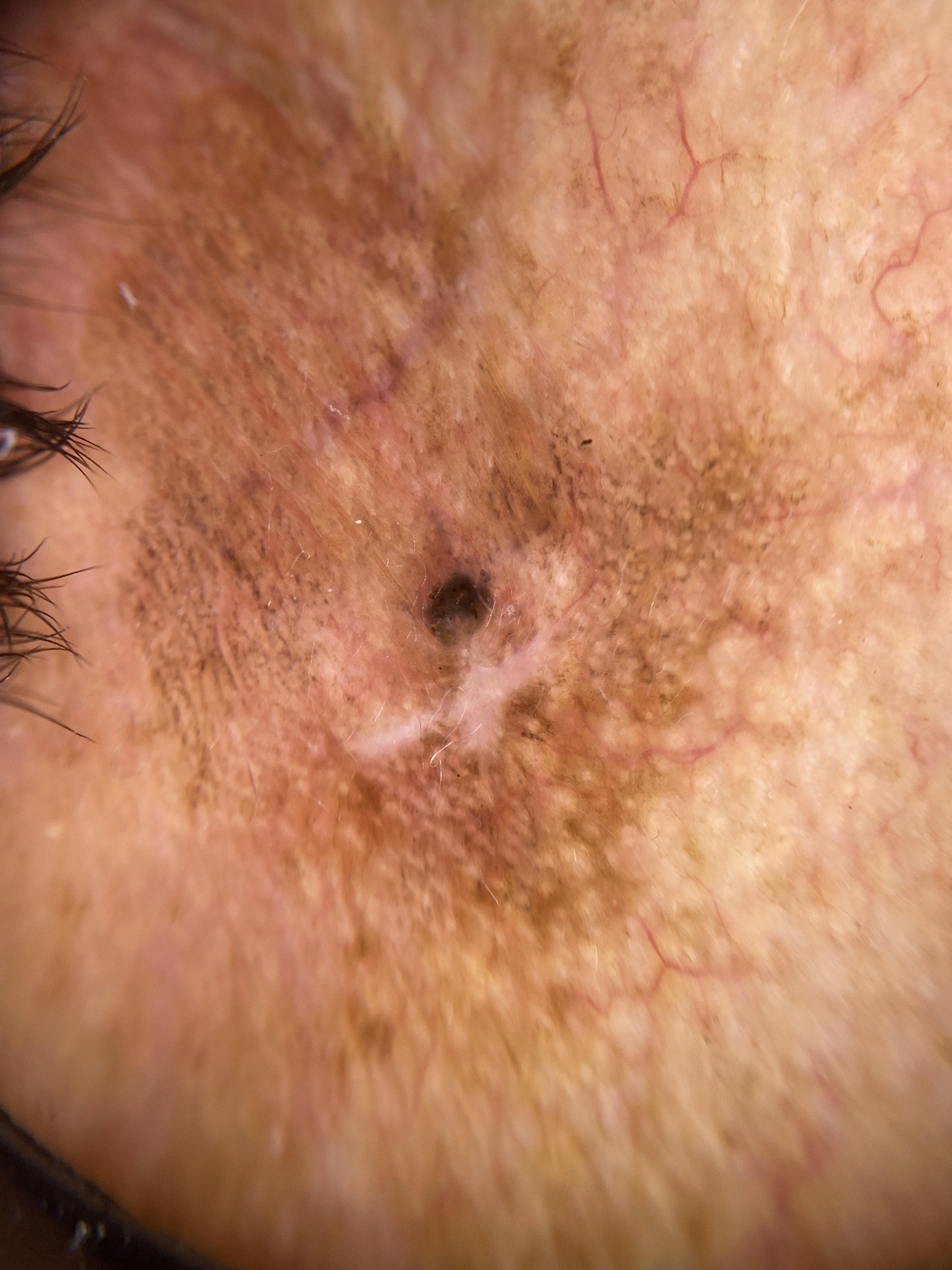A female patient in their mid- to late 80s or older. A skin lesion imaged with contact-polarized dermoscopy. The lesion is on the head or neck. Histopathologically confirmed as a squamous cell carcinoma.